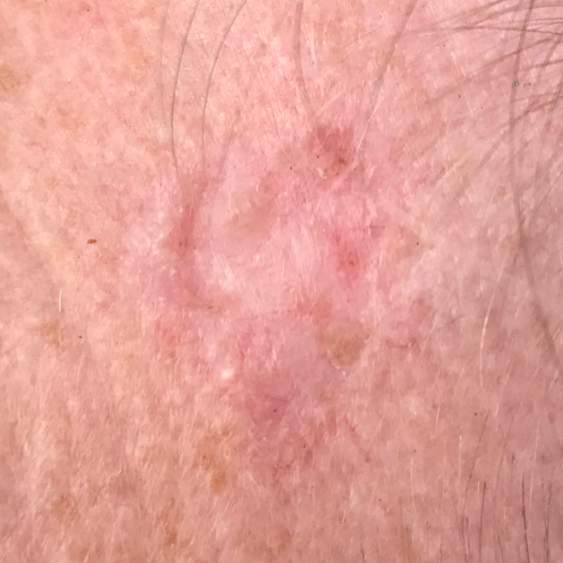Clinical context: FST III. By history, alcohol use and prior malignancy (patient or family). A female subject in their 50s. The lesion involves the face. The lesion measures approximately 15 × 10 mm. By the patient's account, the lesion is elevated, has grown, has bled, and has changed. Pathology: The biopsy diagnosis was a basal cell carcinoma.